This image was taken at an angle.
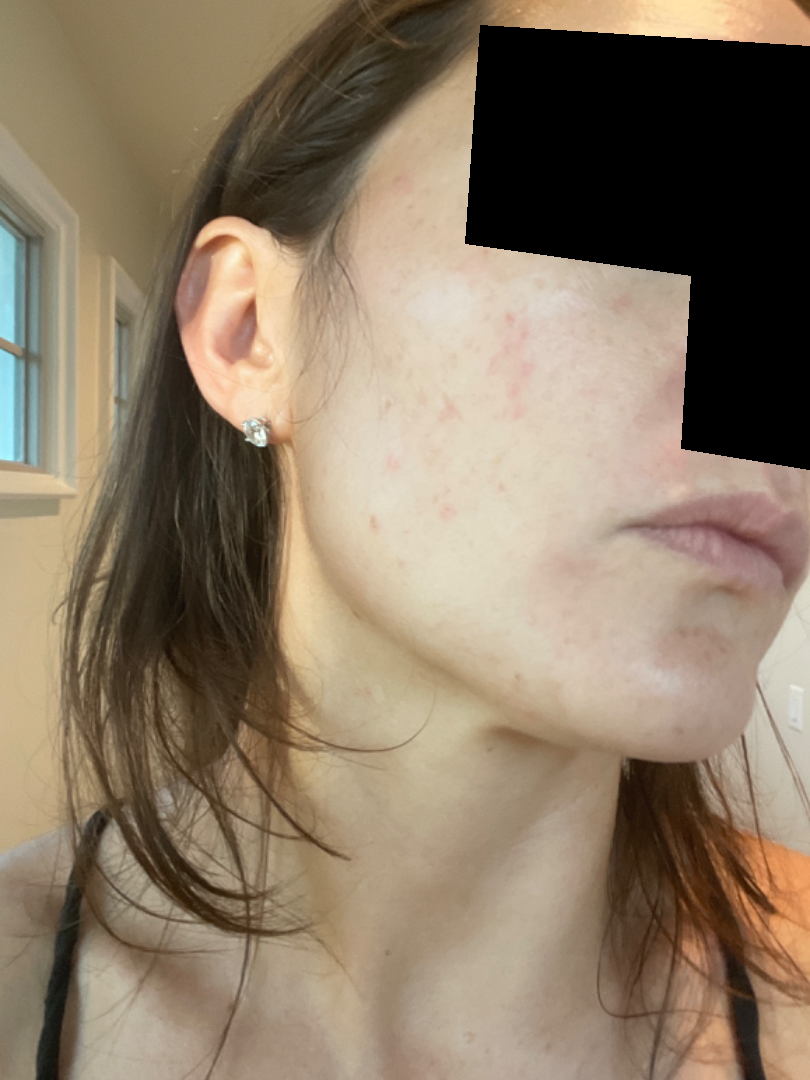Present for about one day. The patient described the issue as a rash. The lesion is associated with itching. The patient reported no systemic symptoms. On dermatologist assessment of the image, the leading consideration is Acne; an alternative is Rosacea; also consider Perioral Dermatitis.